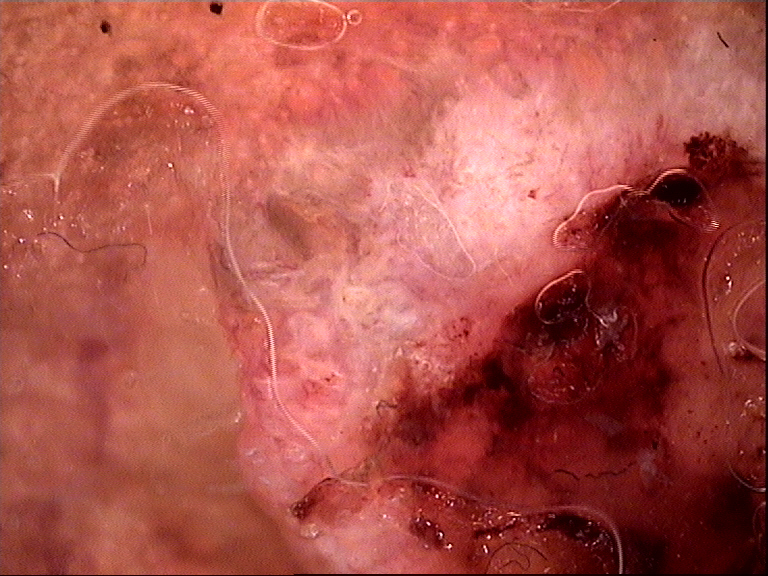Q: What is the imaging modality?
A: dermatoscopy
Q: What is this lesion?
A: squamous cell carcinoma (biopsy-proven)